The chart records alcohol use and prior malignancy (patient or family). A smartphone photograph of a skin lesion. A male patient in their 70s.
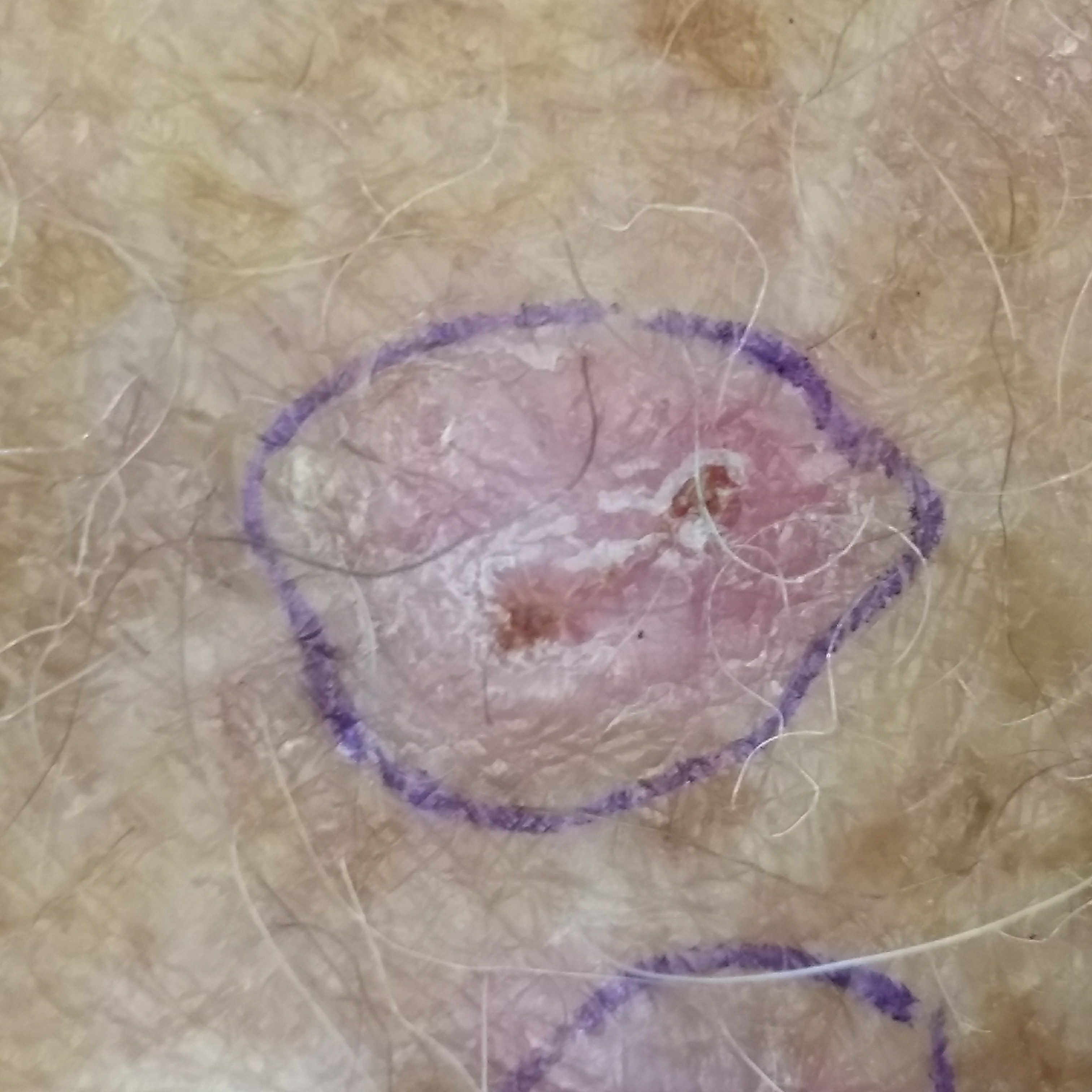{"lesion_location": "a forearm", "lesion_size": {"diameter_1_mm": 6.0, "diameter_2_mm": 5.0}, "symptoms": {"present": ["itching", "bleeding"]}, "diagnosis": {"name": "actinic keratosis", "code": "ACK", "malignancy": "indeterminate", "confirmation": "clinical consensus"}}